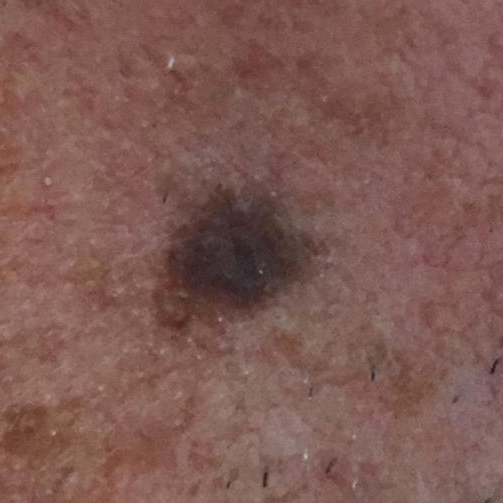A patient in their 50s.
Located on the face.
The patient reports that the lesion has grown.
Clinically diagnosed as a seborrheic keratosis.